A clinical photo of a skin lesion taken with a smartphone:
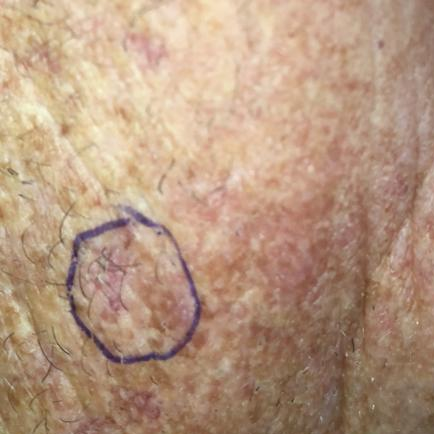The lesion is located on the neck.
The clinical impression was a lesion with uncertain malignant potential — an actinic keratosis.